An image taken at an angle; the affected area is the leg: 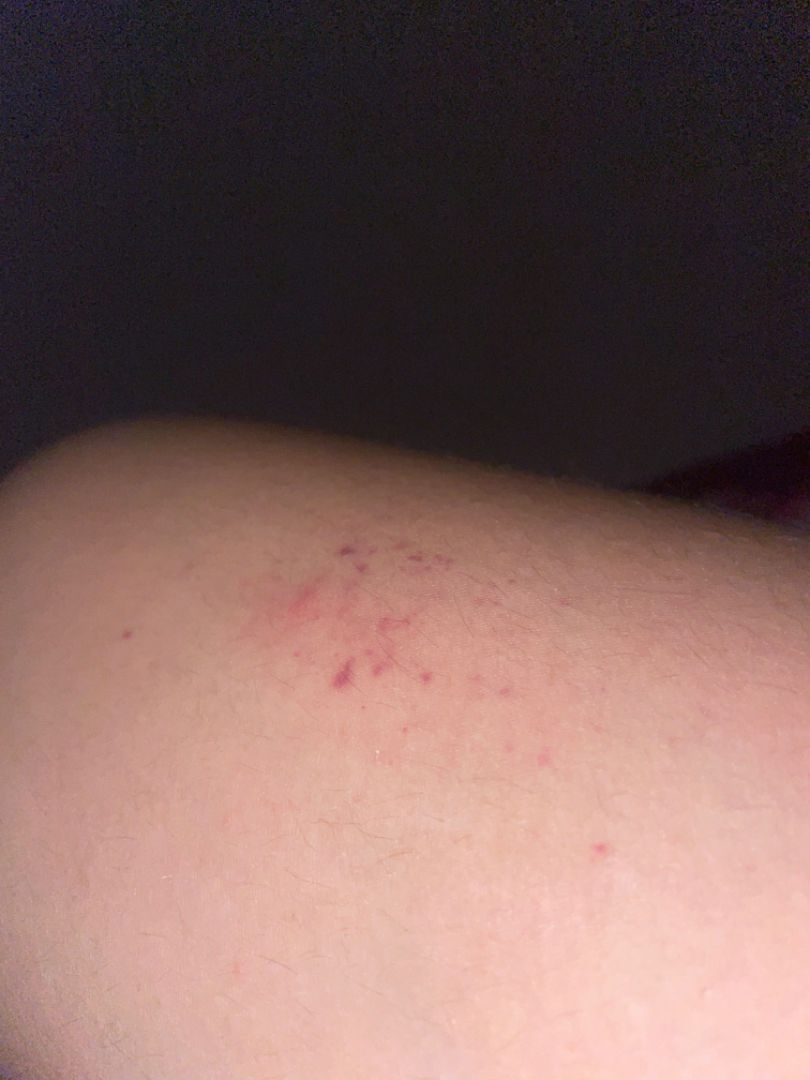The reviewer was unable to grade this case for skin condition.